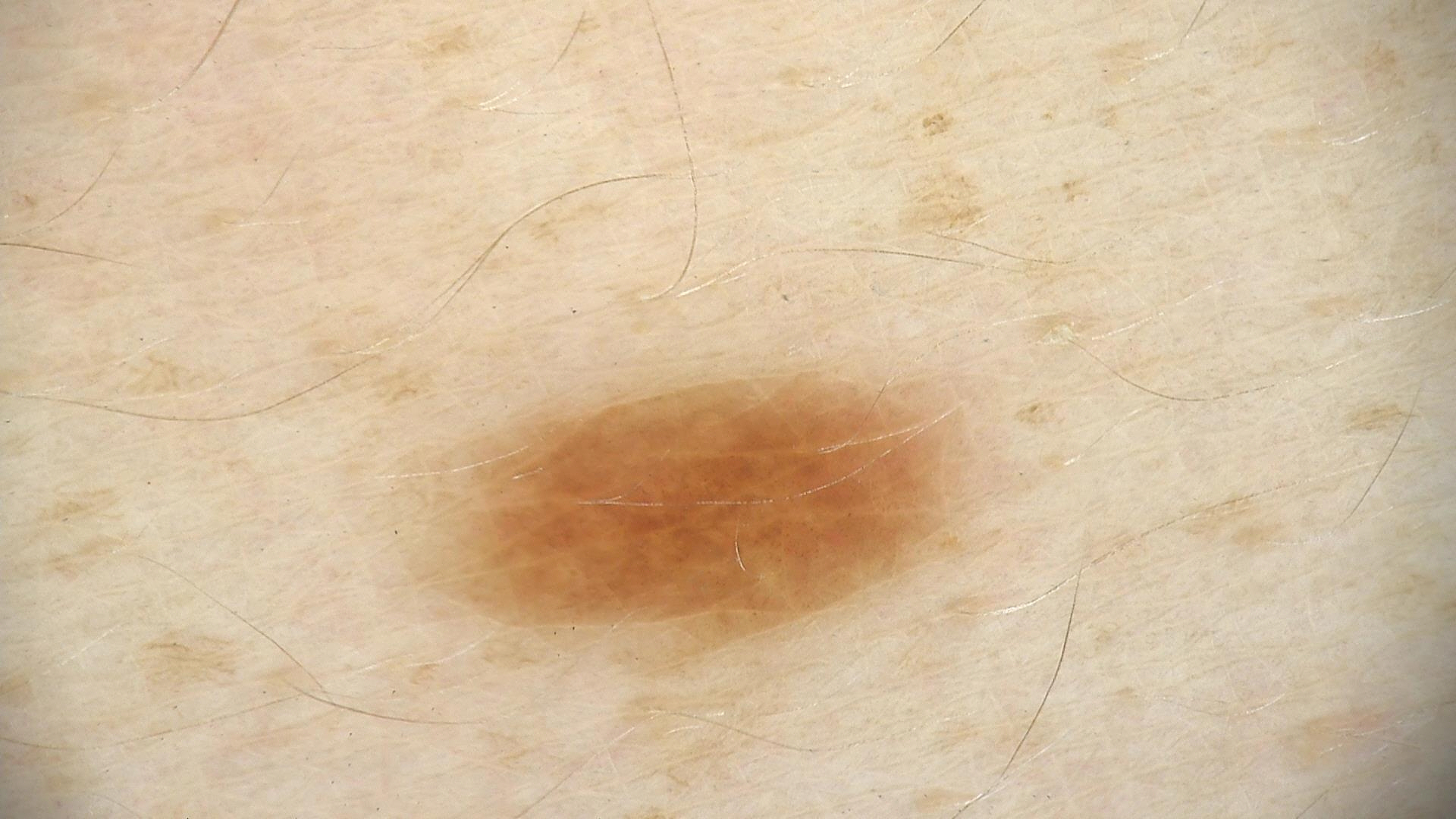Classified as a dysplastic junctional nevus.